The contributor is 18–29, male · the photograph is a close-up of the affected area · reported duration is less than one week · the back of the hand is involved · texture is reported as fluid-filled and raised or bumpy · the contributor reports itching and bothersome appearance:
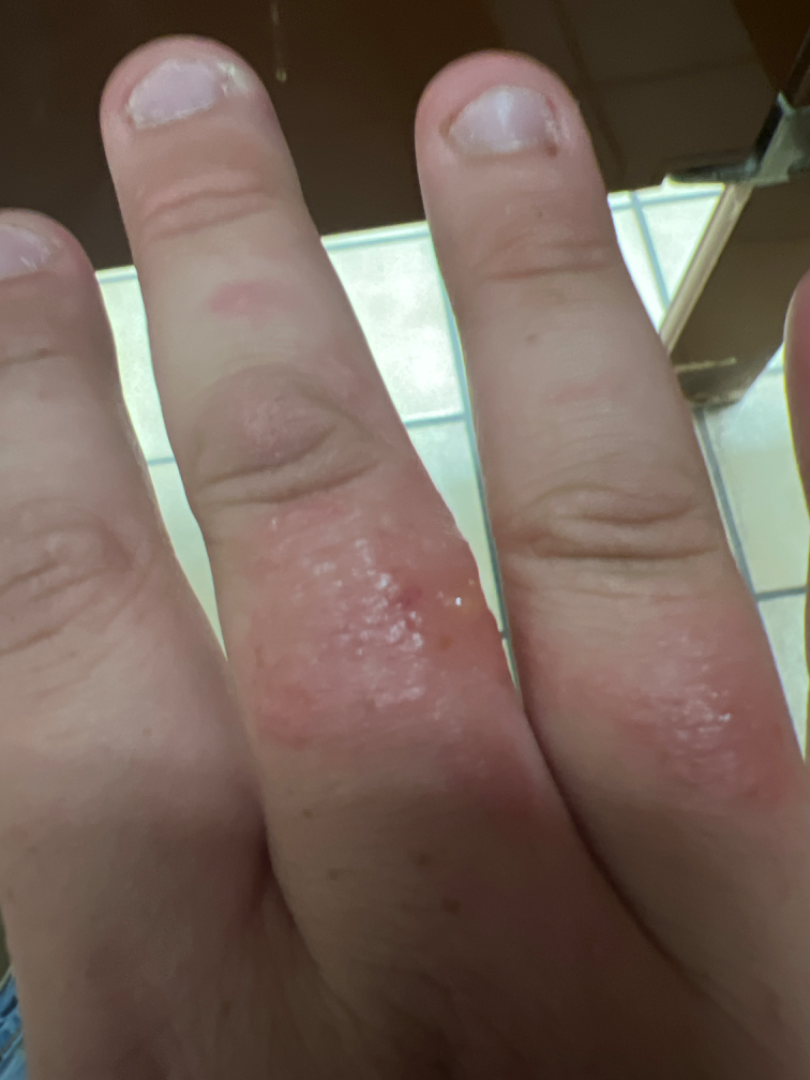| key | value |
|---|---|
| assessment | Burn of skin and Allergic Contact Dermatitis were each considered, in no particular order; a remote consideration is Impetigo |